A skin lesion imaged with a dermatoscope:
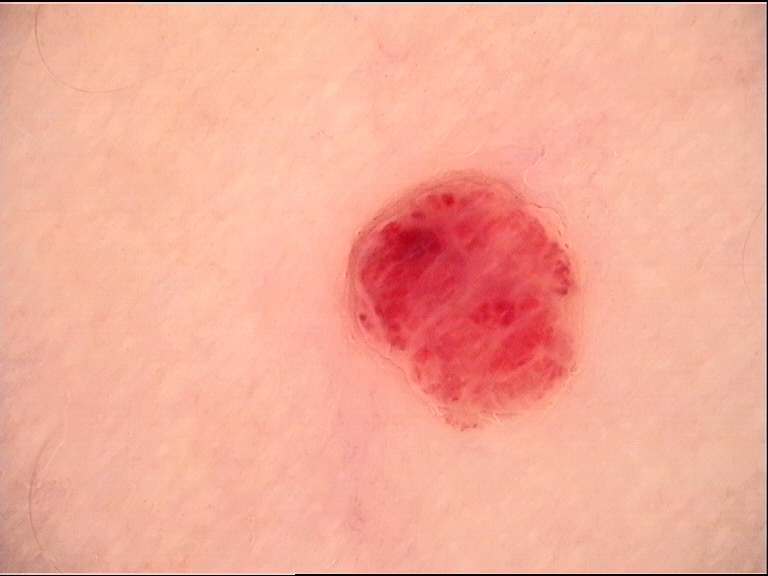Impression: Diagnosed as a hemangioma.